Recorded as Fitzpatrick skin type III; a male patient aged 72 — 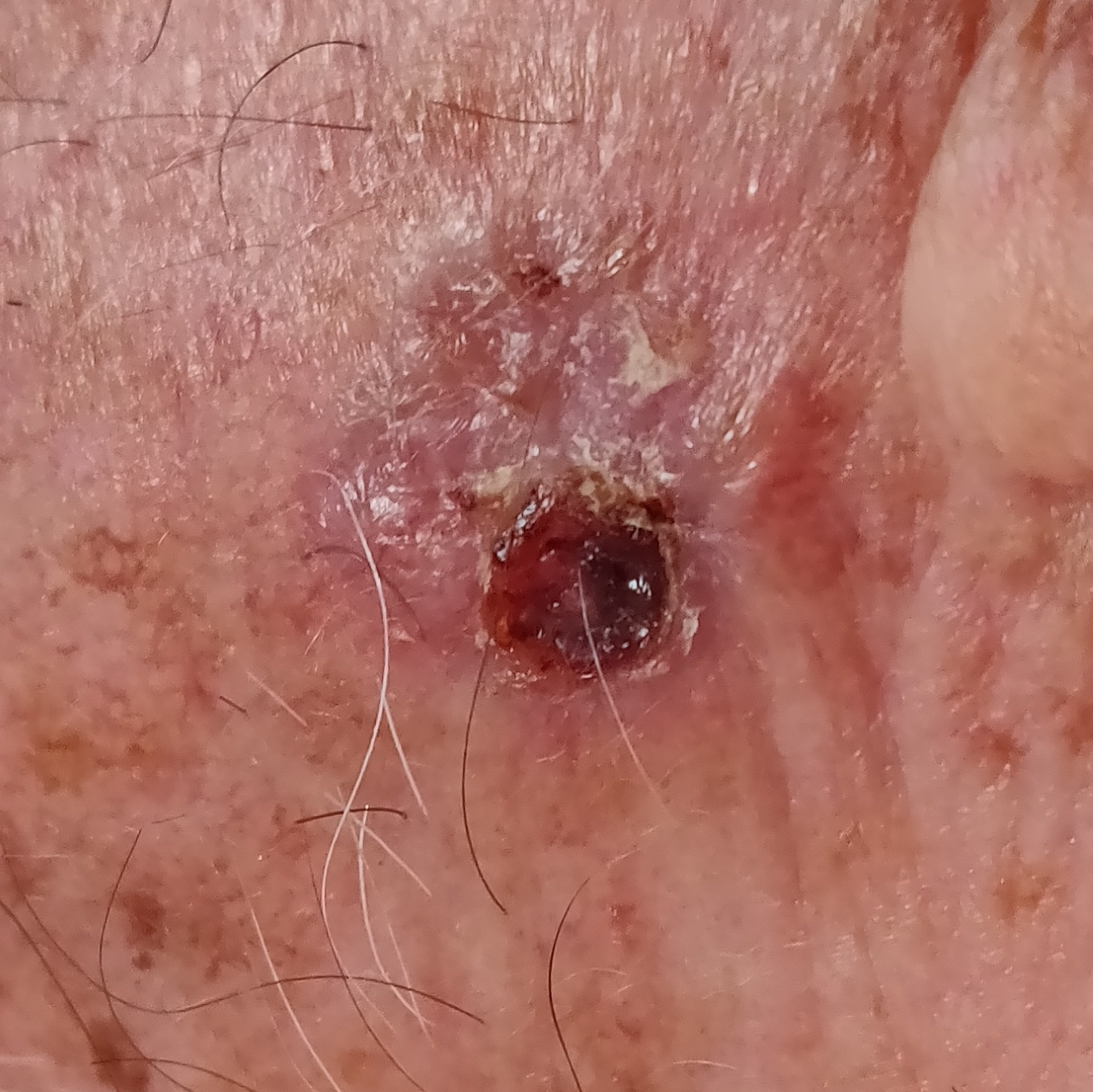body site=the face
diameter=approx. 17 × 14 mm
patient-reported symptoms=bleeding, itching, growth, change in appearance, elevation / no pain
diagnostic label=basal cell carcinoma (biopsy-proven)